A skin lesion imaged with a dermatoscope.
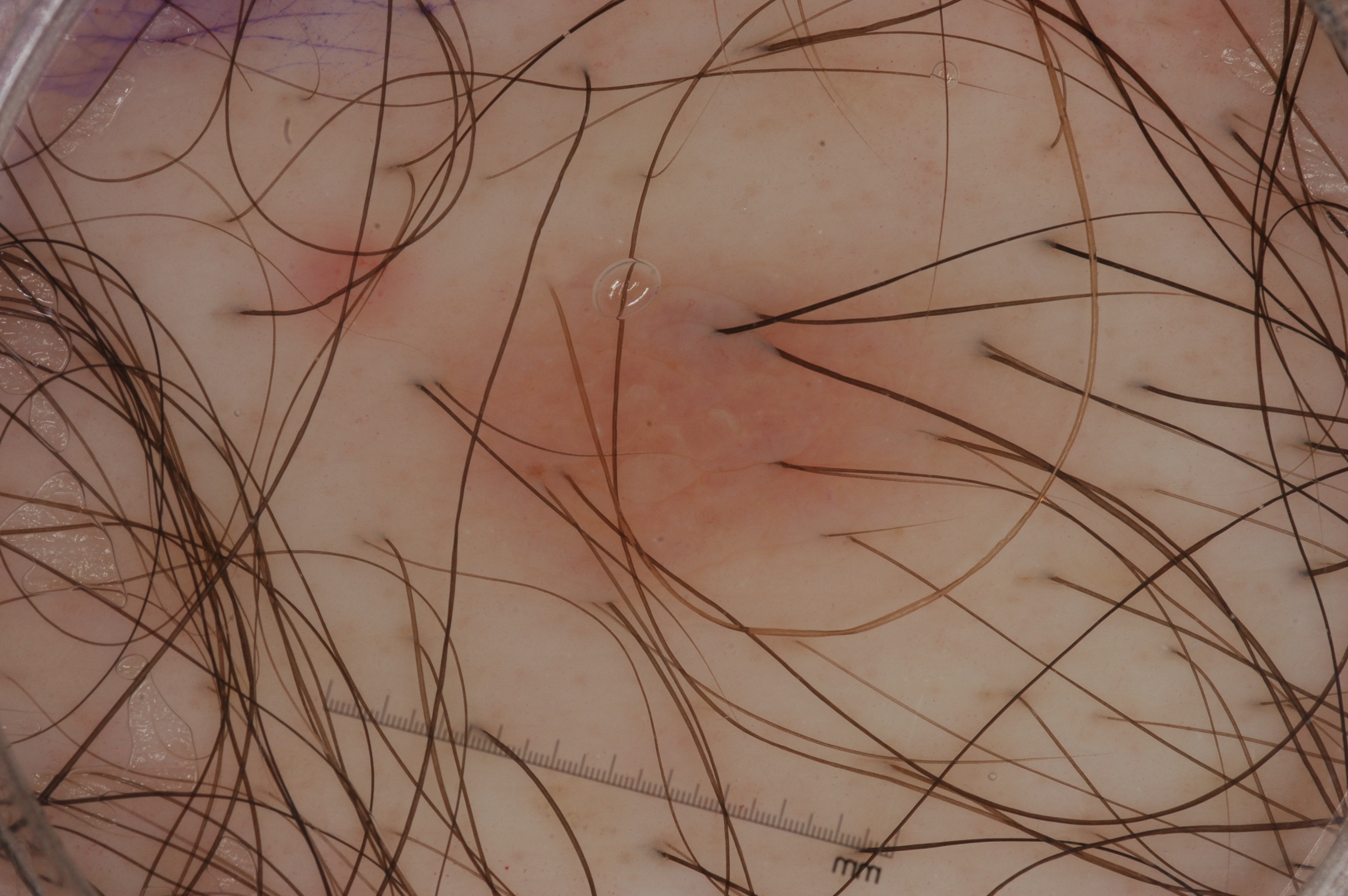| field | value |
|---|---|
| lesion extent | moderate |
| bounding box | 447 254 987 607 |
| absent dermoscopic findings | streaks, milia-like cysts, pigment network, and negative network |
| diagnosis | a melanocytic nevus, a benign lesion |